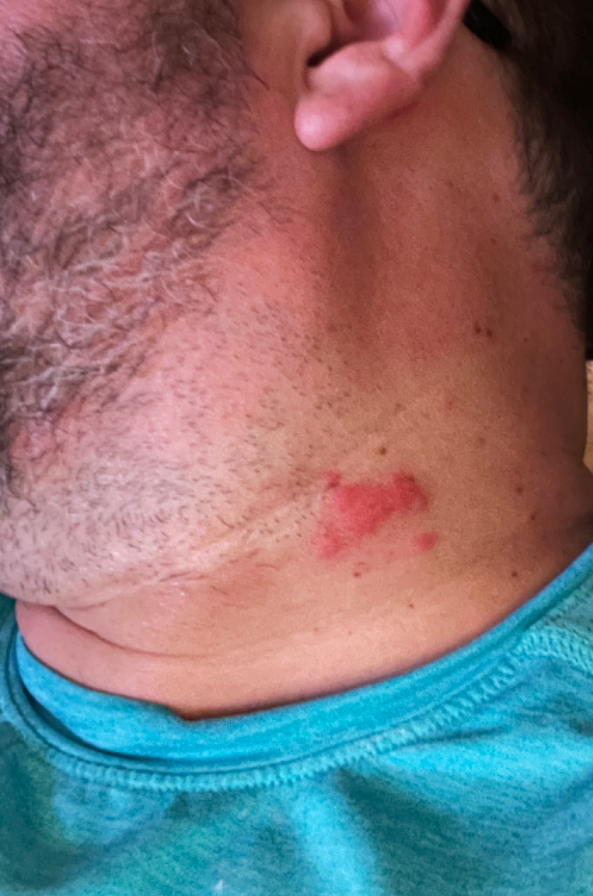symptom duration — about one day
subject — male
symptoms — bothersome appearance and itching
site — head or neck
view — at an angle
impression — B-Cell Cutaneous Lymphoma (leading); Dermatofibrosarcoma protuberans (possible); Urticaria (remote)